A dermoscopic view of a skin lesion; a male subject aged 38-42 — 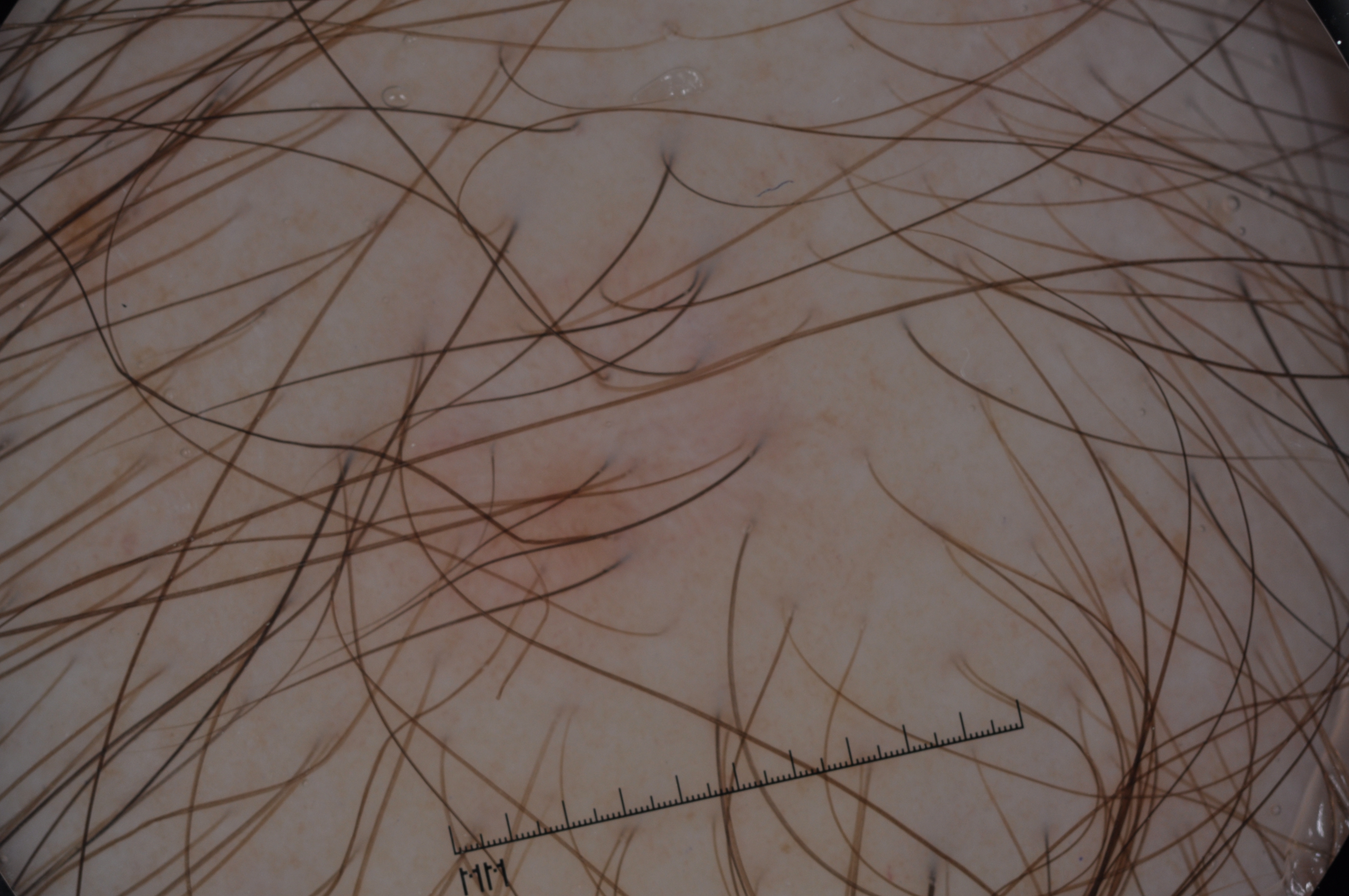Findings:
– dermoscopic features assessed but absent — streaks, pigment network, negative network, and milia-like cysts
– extent — ~13% of the field
– bounding box — box(312, 209, 825, 627)
– diagnostic label — a melanocytic nevus, a benign skin lesion